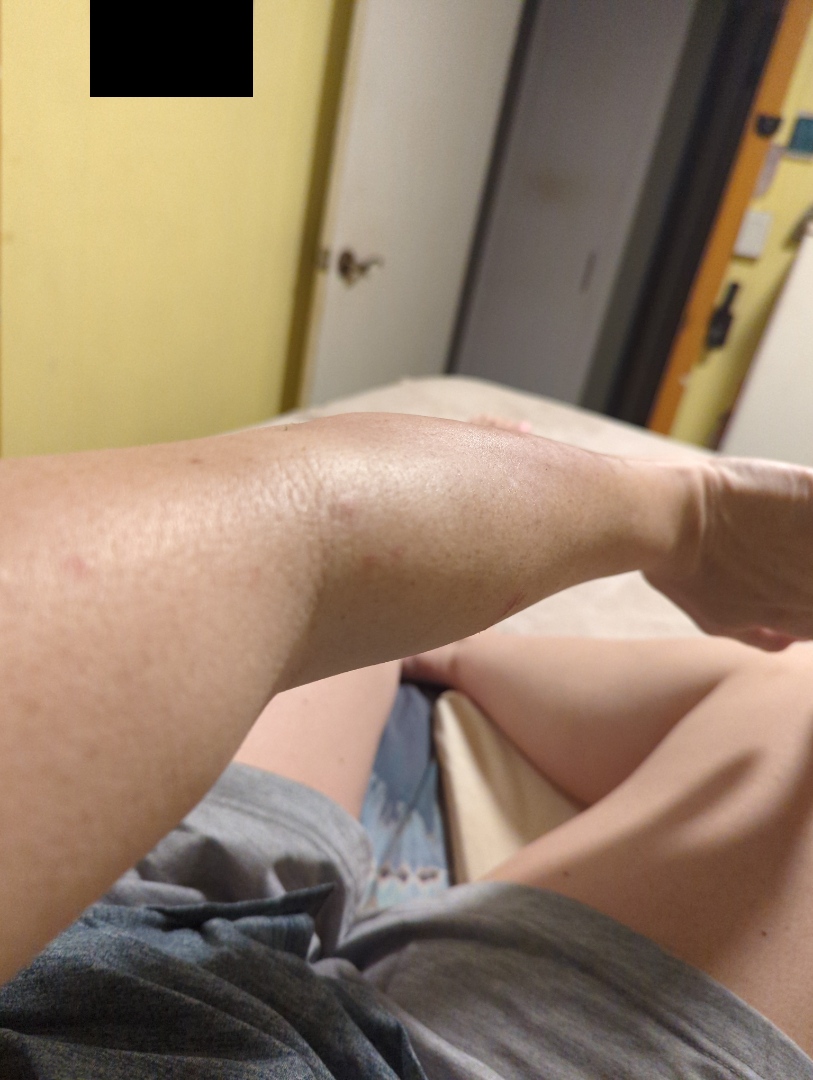assessment = indeterminate | shot type = at a distance | subject = female, age 40–49 | location = arm.